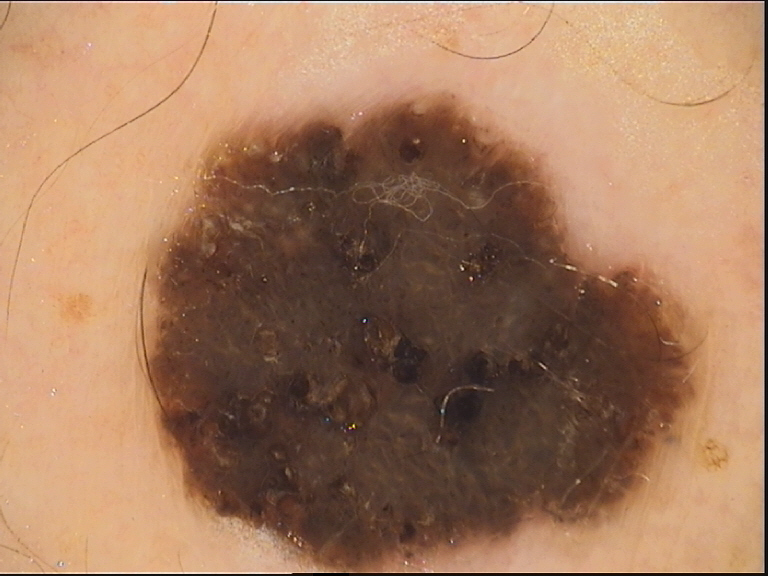image: dermatoscopy
diagnosis:
  name: seborrheic keratosis
  code: sk
  malignancy: benign
  super_class: non-melanocytic
  confirmation: expert consensus